Texture is reported as flat; the subject is 18–29, female; a close-up photograph; the patient considered this a rash; the contributor notes bothersome appearance and itching; the condition has been present for about one day; the back of the torso and leg are involved; the patient reported no systemic symptoms:
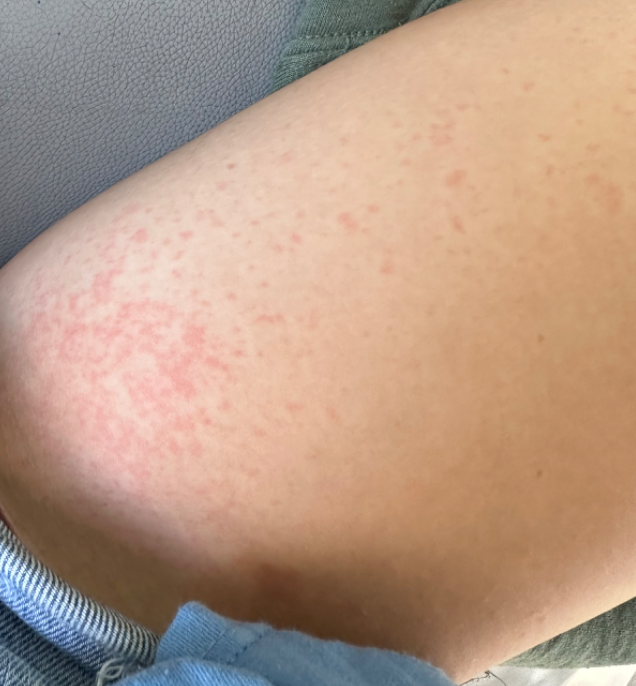assessment = could not be assessed.